Close-up view · the subject is 18–29, female · the back of the torso is involved — 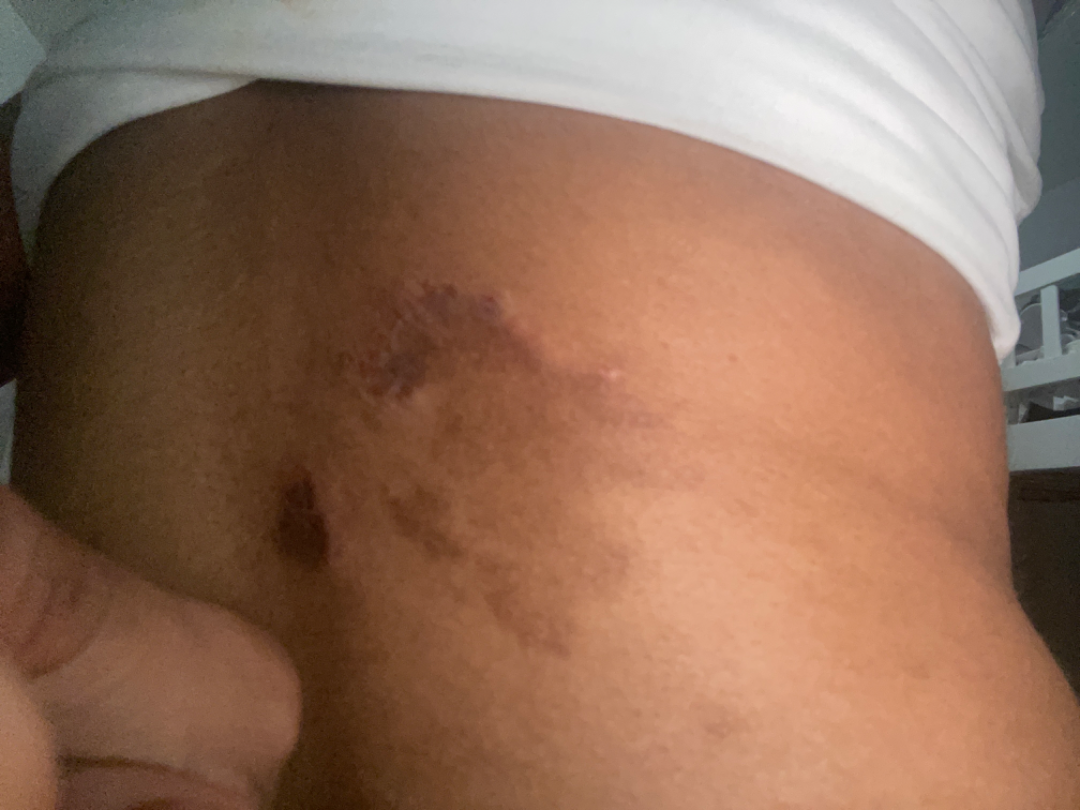assessment: ungradable on photographic review